A female subject about 65 years old · a dermoscopic image of a skin lesion: 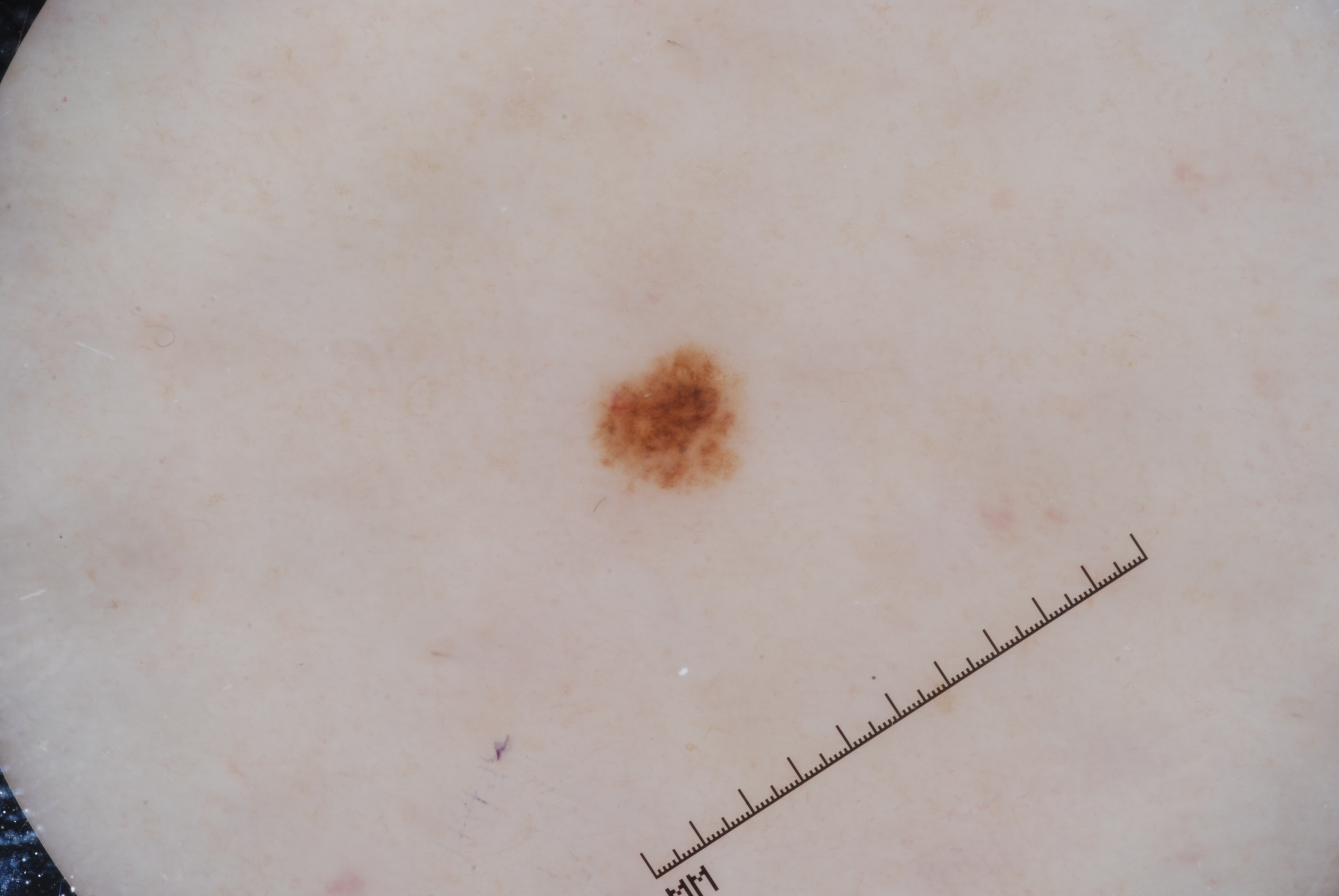The lesion covers approximately 2% of the dermoscopic field. As (left, top, right, bottom), the lesion spans [588, 340, 748, 497]. Dermoscopic review identifies pigment network. The diagnostic assessment was a melanocytic nevus.